Dermoscopy of a skin lesion — 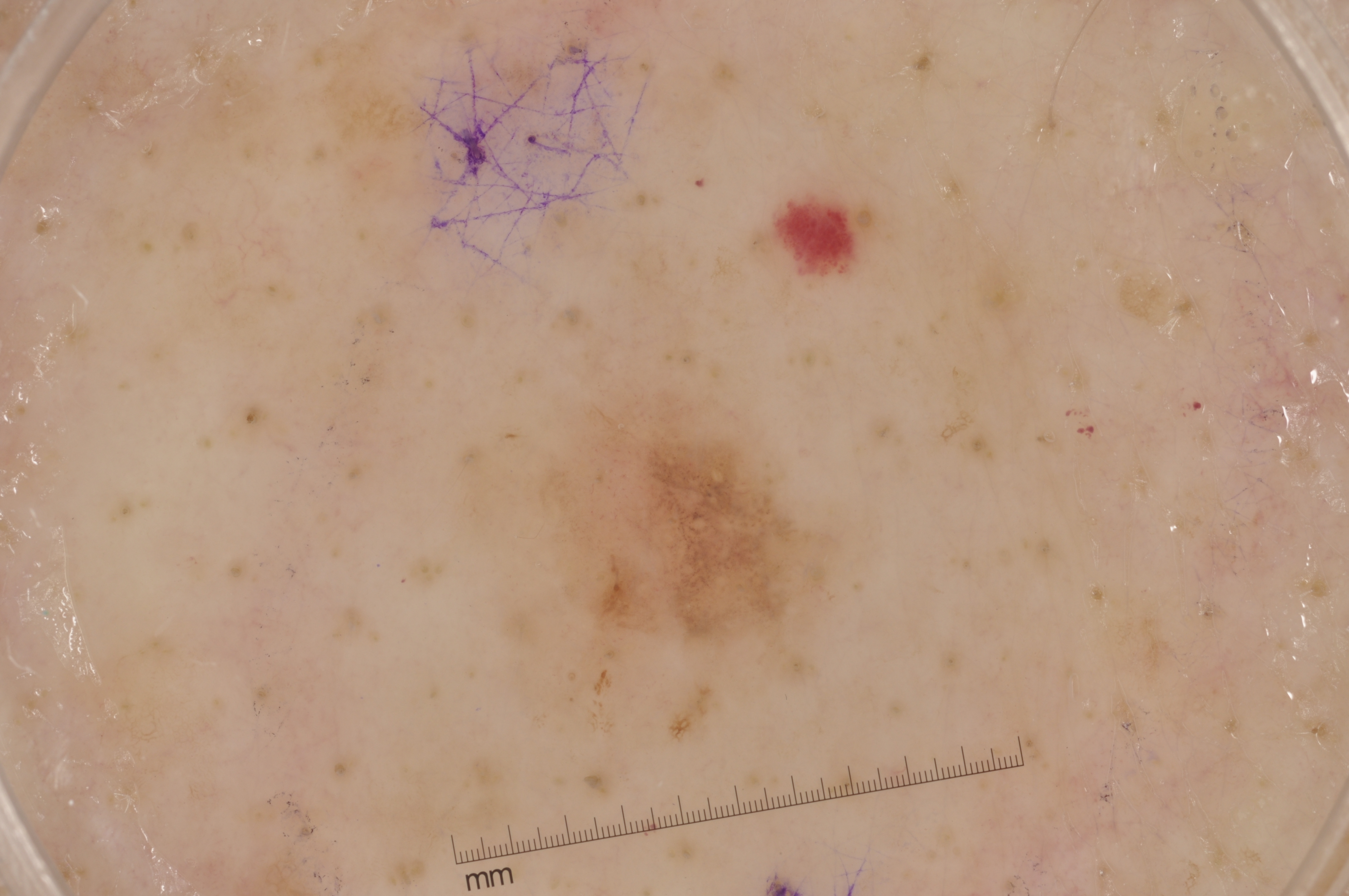On dermoscopy, the lesion shows no negative network, streaks, milia-like cysts, or pigment network.
The lesion covers approximately 5% of the dermoscopic field.
The lesion occupies the region [538, 385, 843, 651].
The biopsy diagnosis was a melanoma.